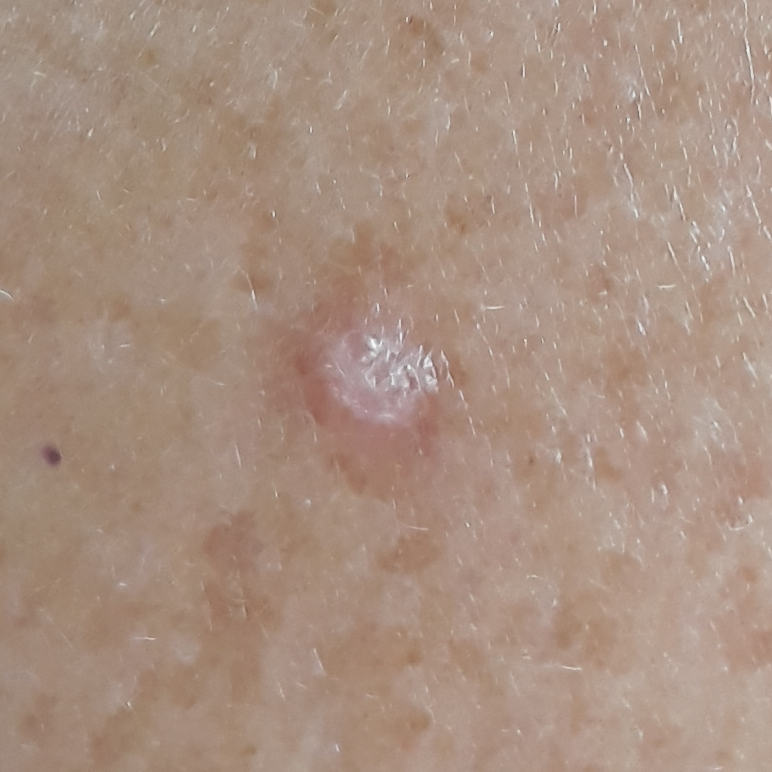Fitzpatrick phototype II. The chart records prior malignancy (patient or family), no tobacco use, and no prior skin cancer (patient or family). A female subject in their 70s. A clinical photograph showing a skin lesion. The lesion measures 7 × 6 mm. The patient describes that the lesion itches and is elevated, but has not changed and has not grown. Diagnosed by dermatologist consensus as an actinic keratosis.